Dermoscopy of a skin lesion.
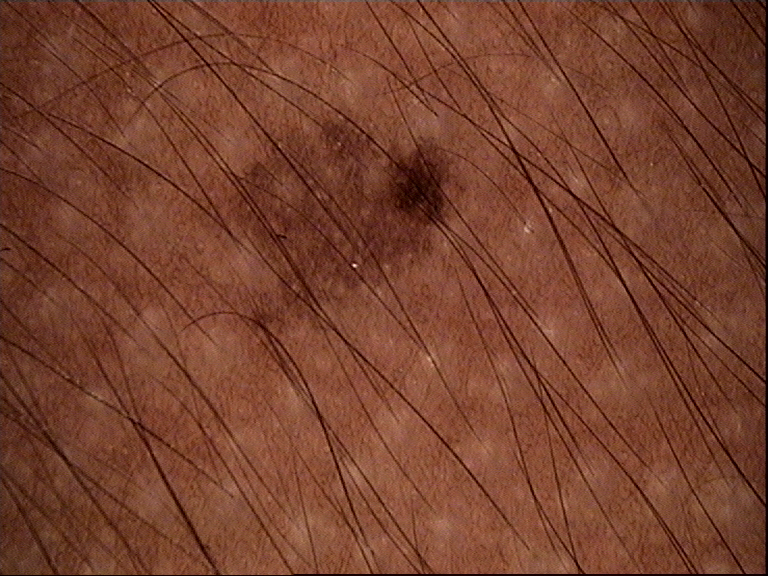Consistent with a dysplastic junctional nevus.